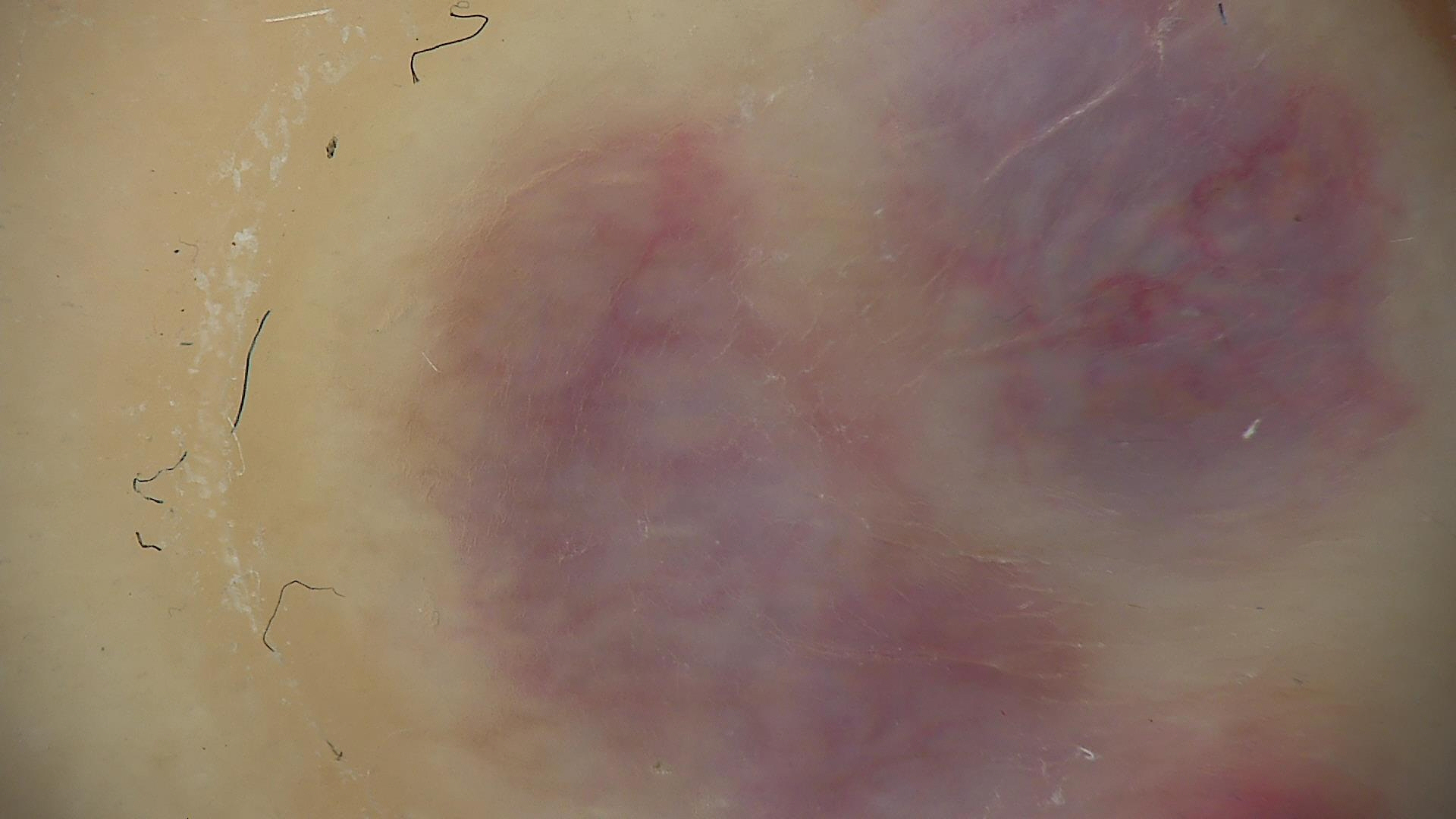– image type: dermoscopy
– pathology: Kaposi sarcoma (biopsy-proven)